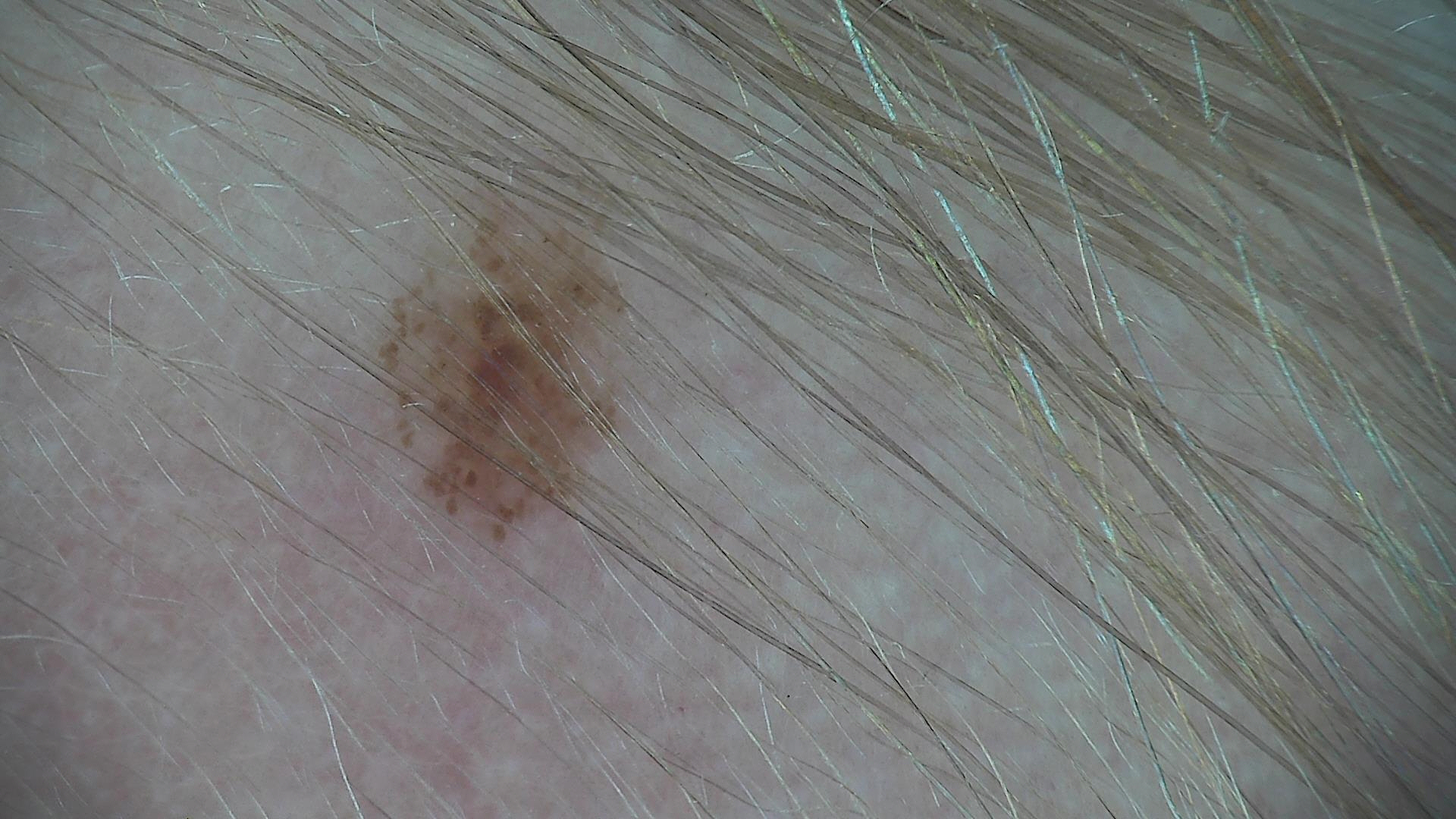A dermoscopic close-up of a skin lesion. Classified as a dysplastic junctional nevus.